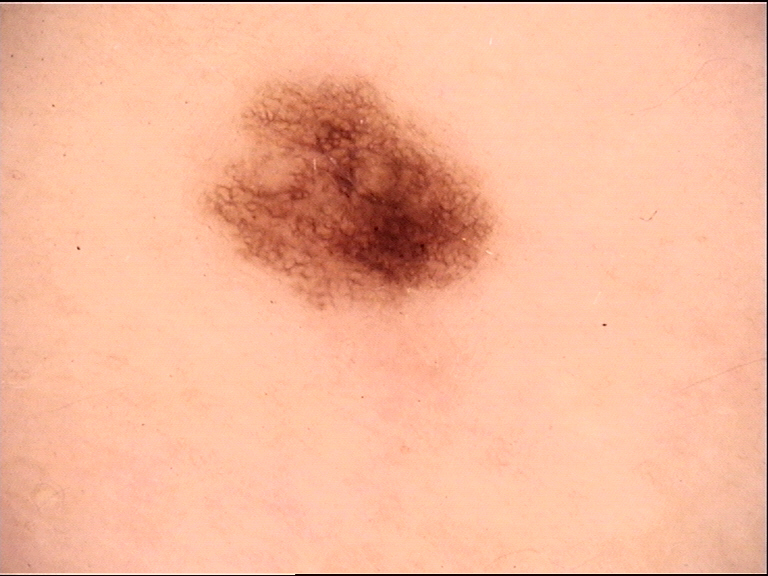Impression: The diagnosis was a benign lesion — a dysplastic junctional nevus.